Female contributor, age 50–59; the affected area is the back of the torso, leg, arm and front of the torso; this is a close-up image.
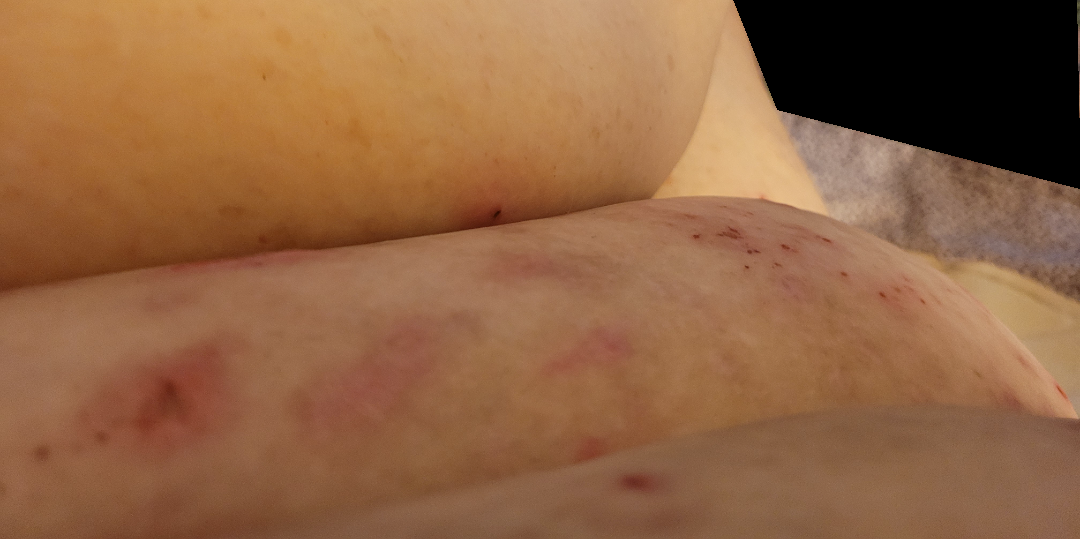Q: What is the differential diagnosis?
A: most likely Prurigo nodularis; also consider Lichen Simplex Chronicus; also on the differential is Pemphigus foliaceus; with consideration of Eczema